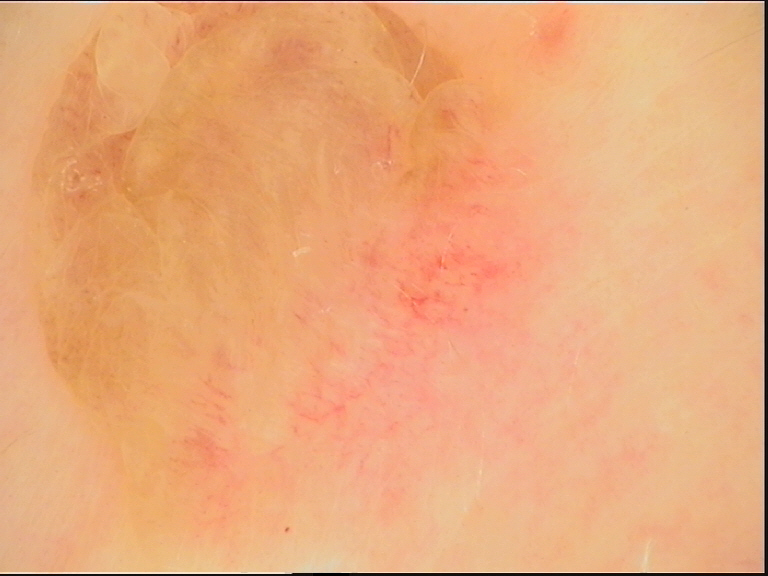Classified as a dermal nevus.